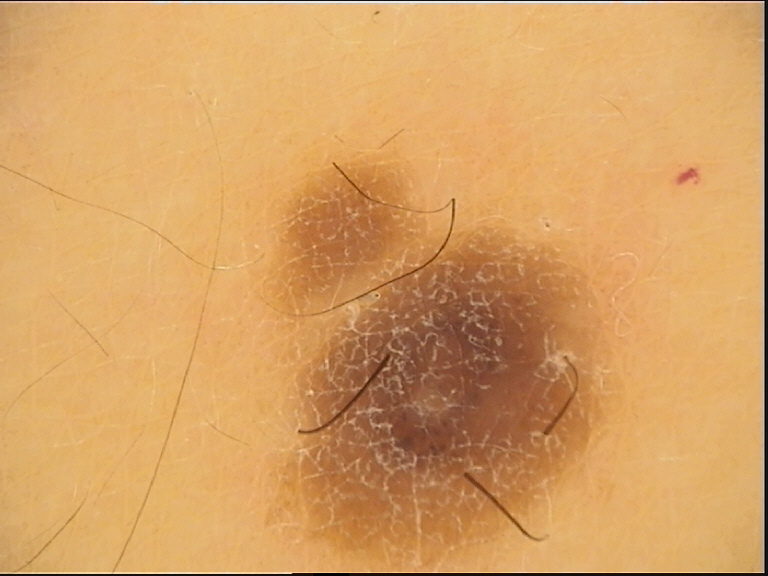imaging = dermoscopy; lesion type = banal; assessment = compound nevus (expert consensus).